The subject is a male aged 70–79. A close-up photograph. The arm is involved:
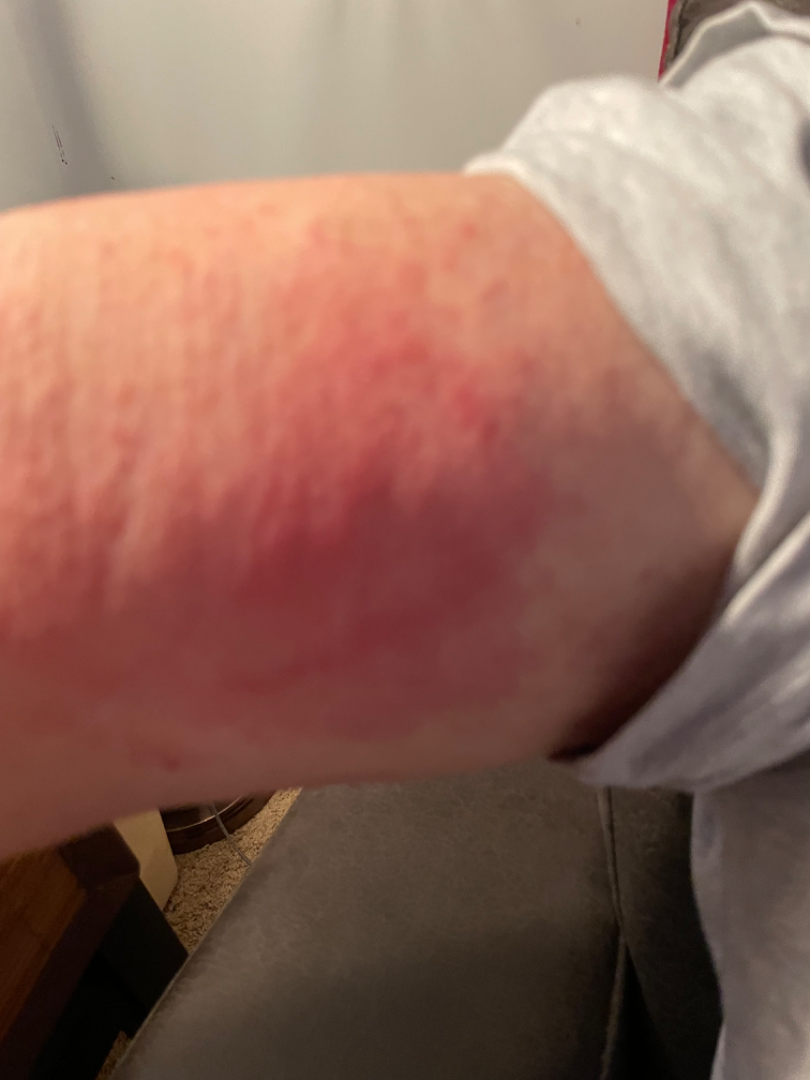differential:
  Allergic Contact Dermatitis: 0.55
  Cellulitis: 0.27
  Urticaria: 0.18